A macroscopic clinical photograph of a skin lesion · a female patient aged 15 · imaged for a research study, with no referral diagnosis recorded · few moles overall by the patient's own estimate · the patient says their skin reddens with sun exposure · the patient reports no personal history of cancer — 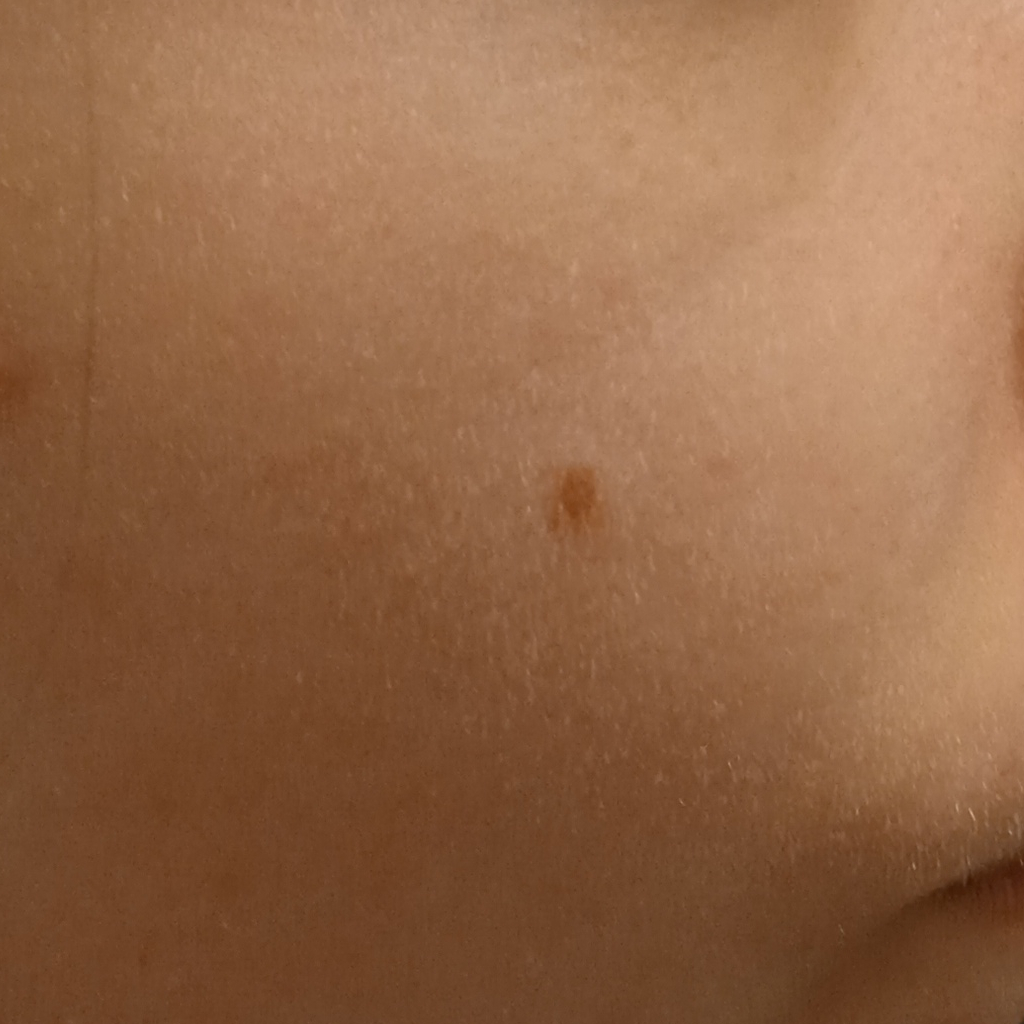body site: the face | lesion size: 3.2 mm | diagnostic label: melanocytic nevus (dermatologist consensus).